A dermoscopy image of a single skin lesion.
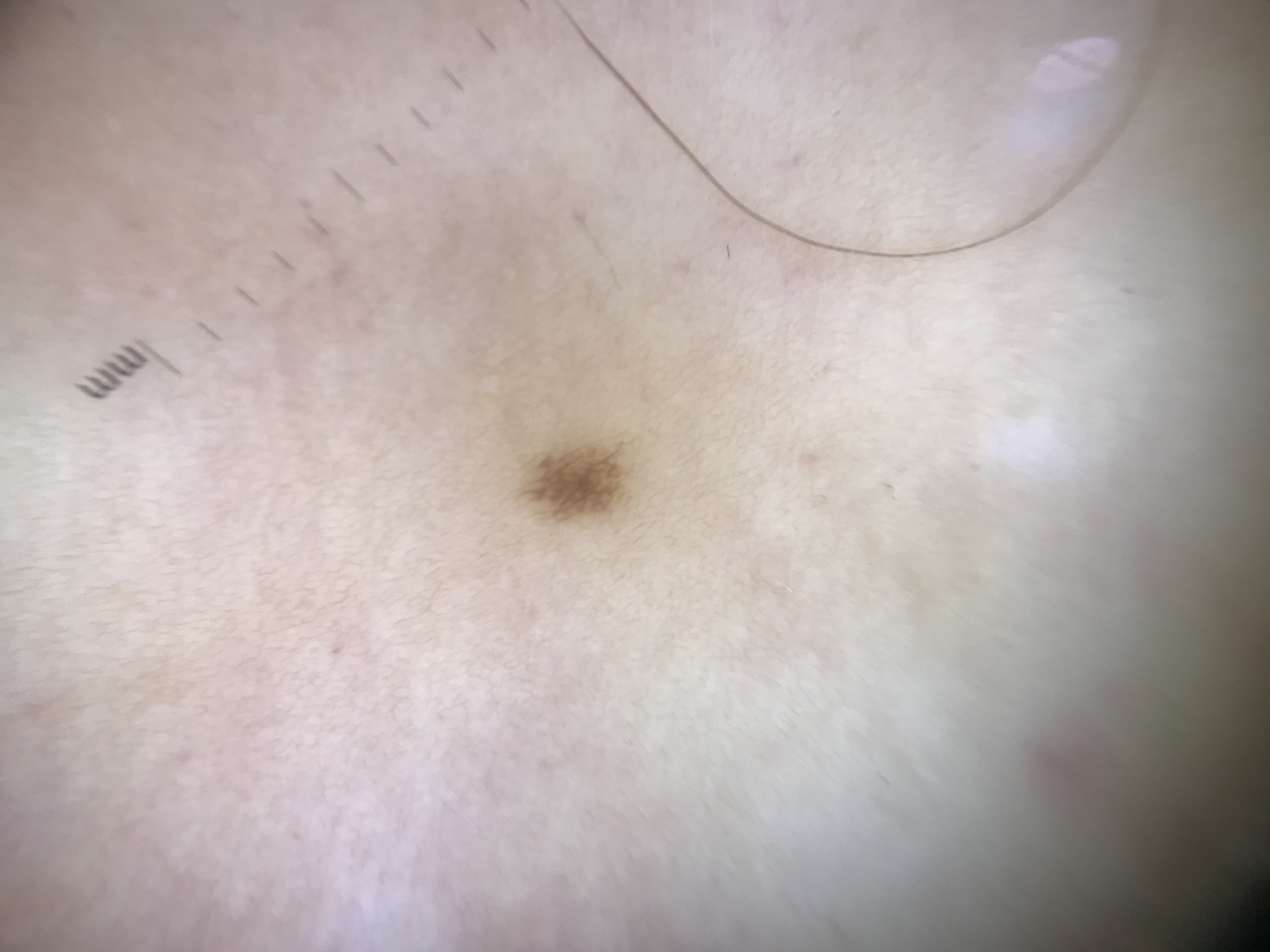diagnosis — junctional nevus (expert consensus).